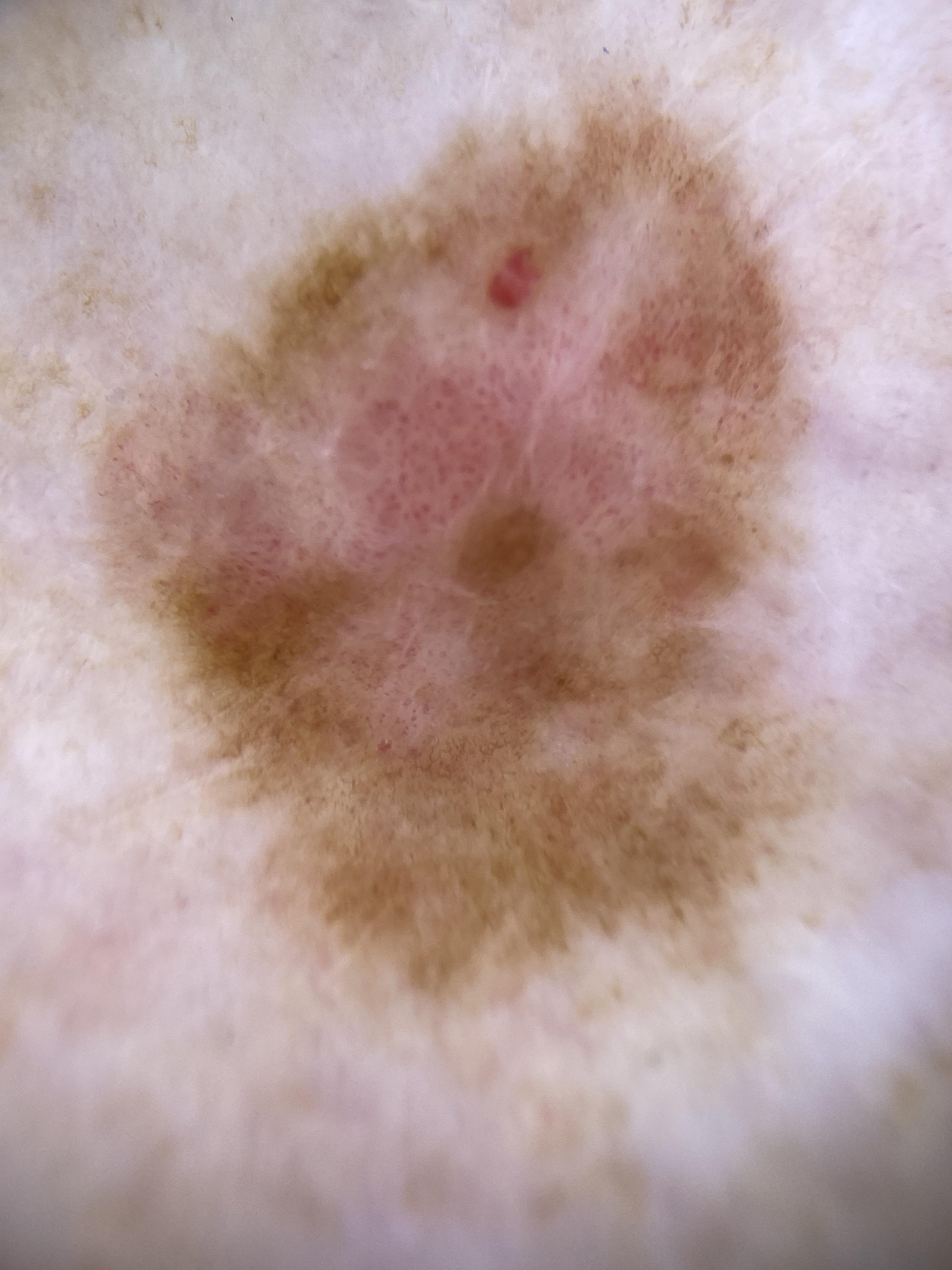A male subject in their mid- to late 70s.
The lesion was found on a lower extremity.
Biopsy-confirmed as a melanoma.